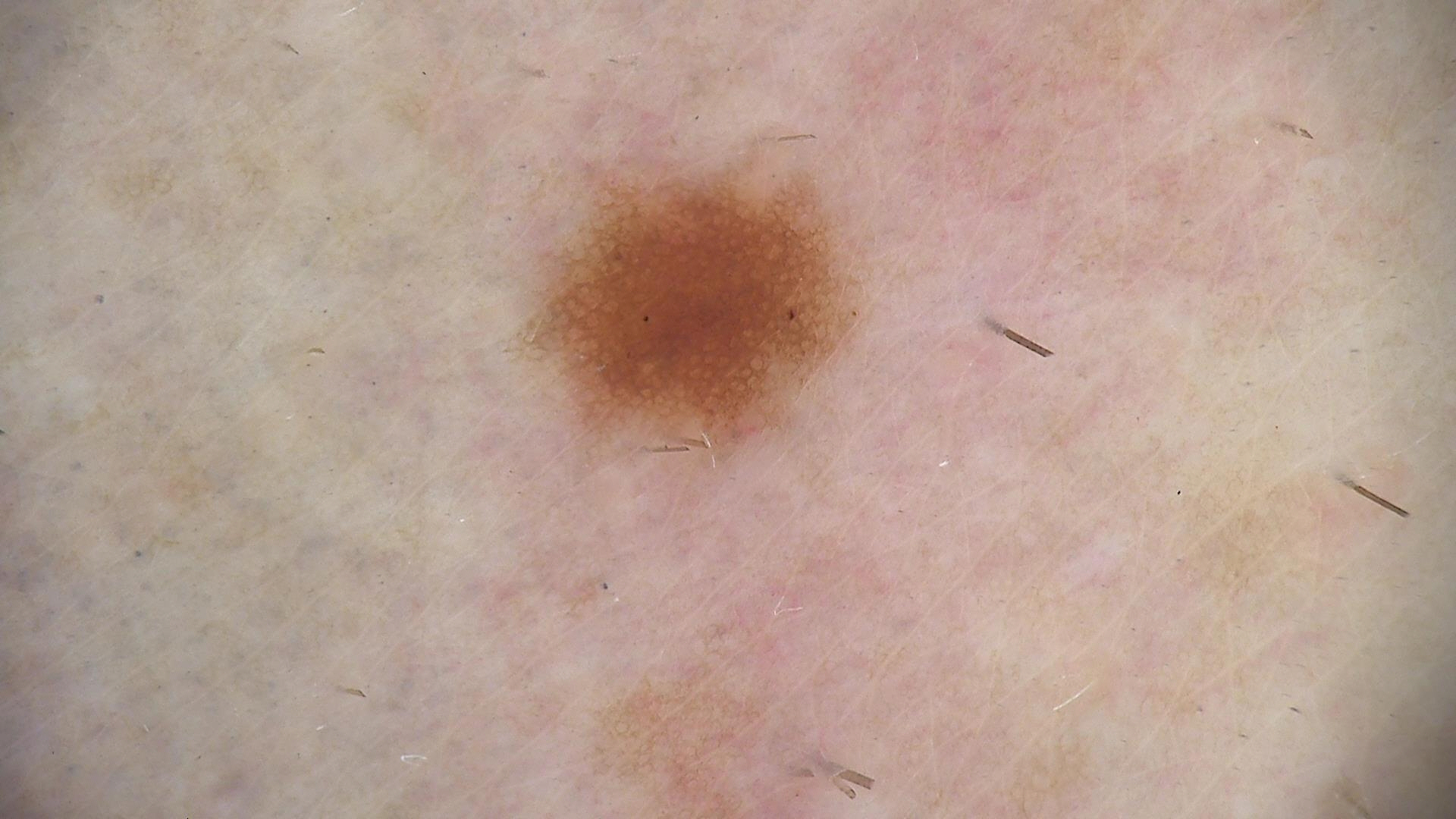Consistent with a benign lesion — a dysplastic junctional nevus.